The photograph is a close-up of the affected area. The front of the torso is involved:
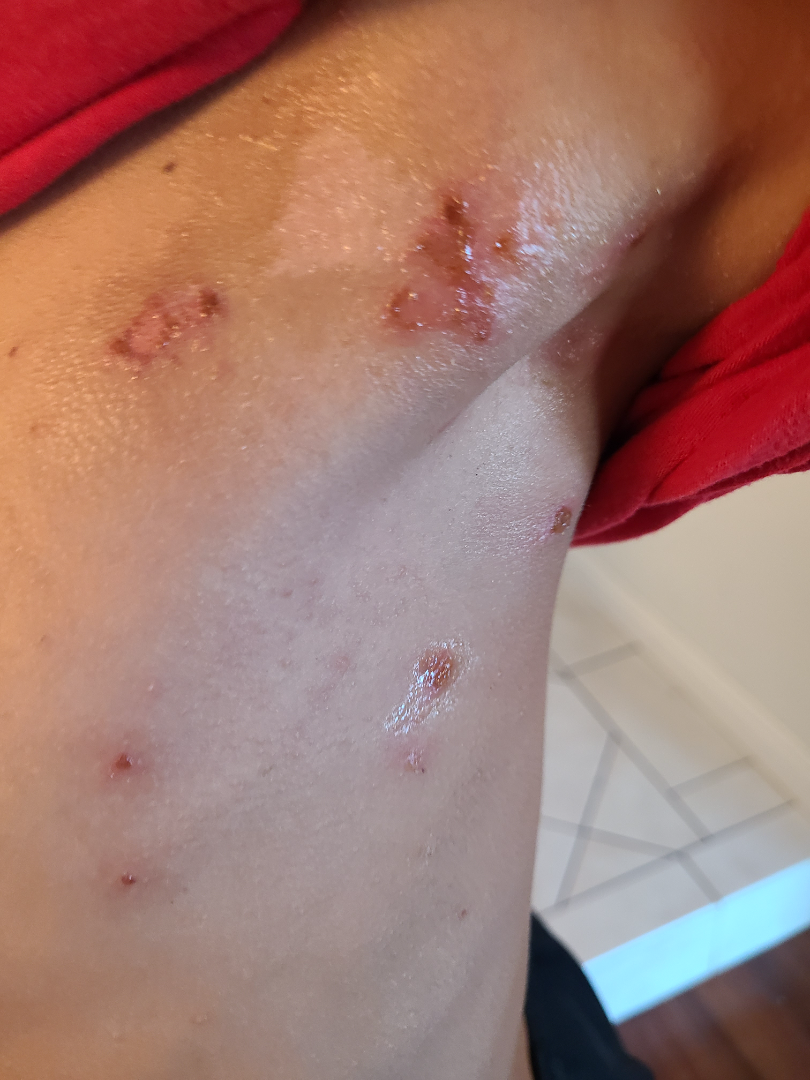duration: one to four weeks
constitutional symptoms: none reported
surface texture: rough or flaky
patient-reported symptoms: bothersome appearance
clinical impression: the differential, in no particular order, includes Impetigo, Pemphigus vulgaris and Linear IgA disease